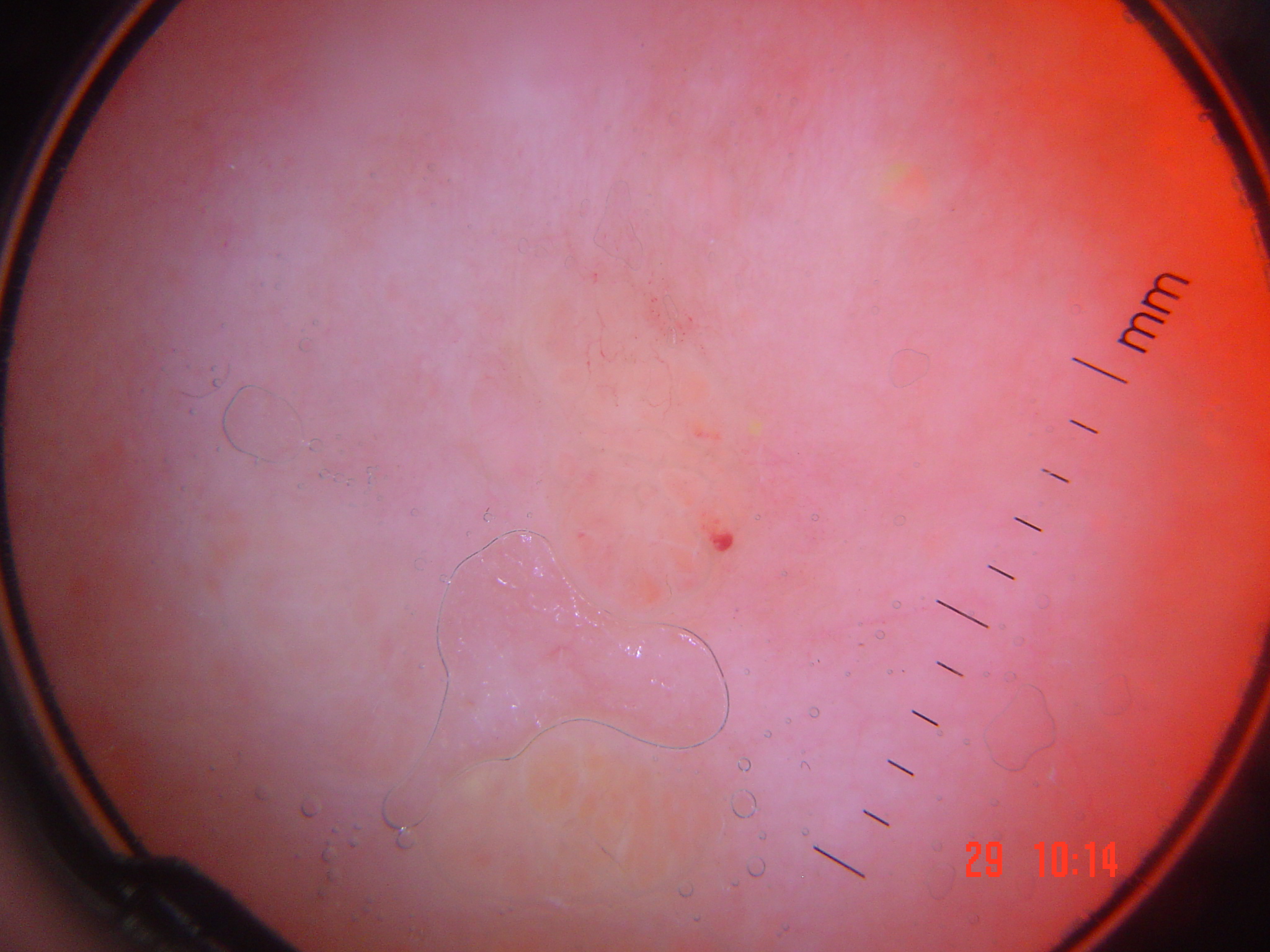modality — dermoscopy
class — lymphangioma (expert consensus)